A dermoscopic close-up of a skin lesion: 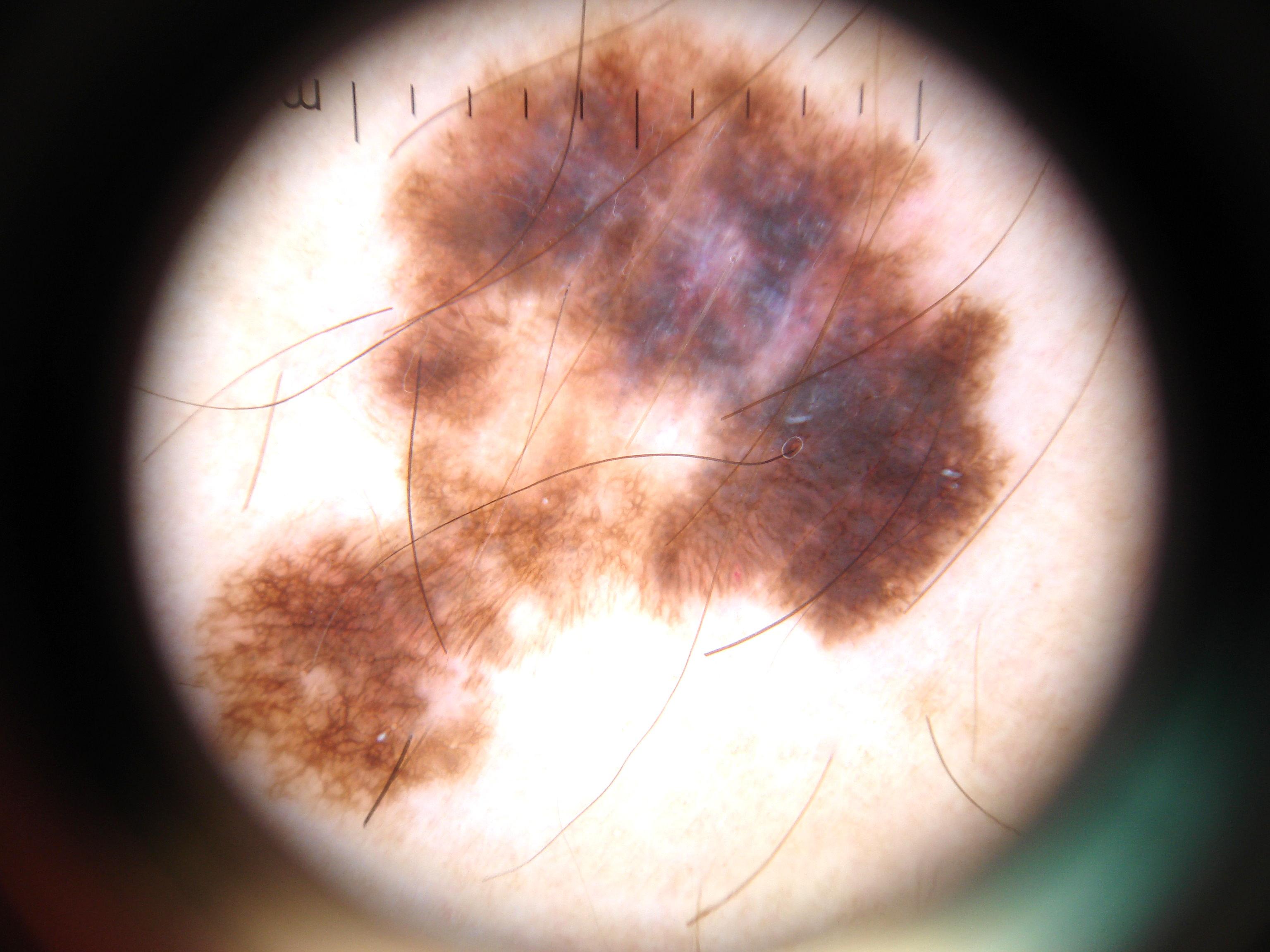<record>
  <dermoscopic_features>
    <present>streaks, pigment network</present>
    <absent>milia-like cysts, globules, negative network</absent>
  </dermoscopic_features>
  <lesion_location>
    <bbox_xyxy>187, 0, 1026, 825</bbox_xyxy>
  </lesion_location>
  <lesion_extent>large</lesion_extent>
  <frame_clip>lesion extends past the field edge</frame_clip>
  <diagnosis>
    <name>melanoma</name>
    <malignancy>malignant</malignancy>
    <lineage>melanocytic</lineage>
    <provenance>histopathology</provenance>
  </diagnosis>
</record>